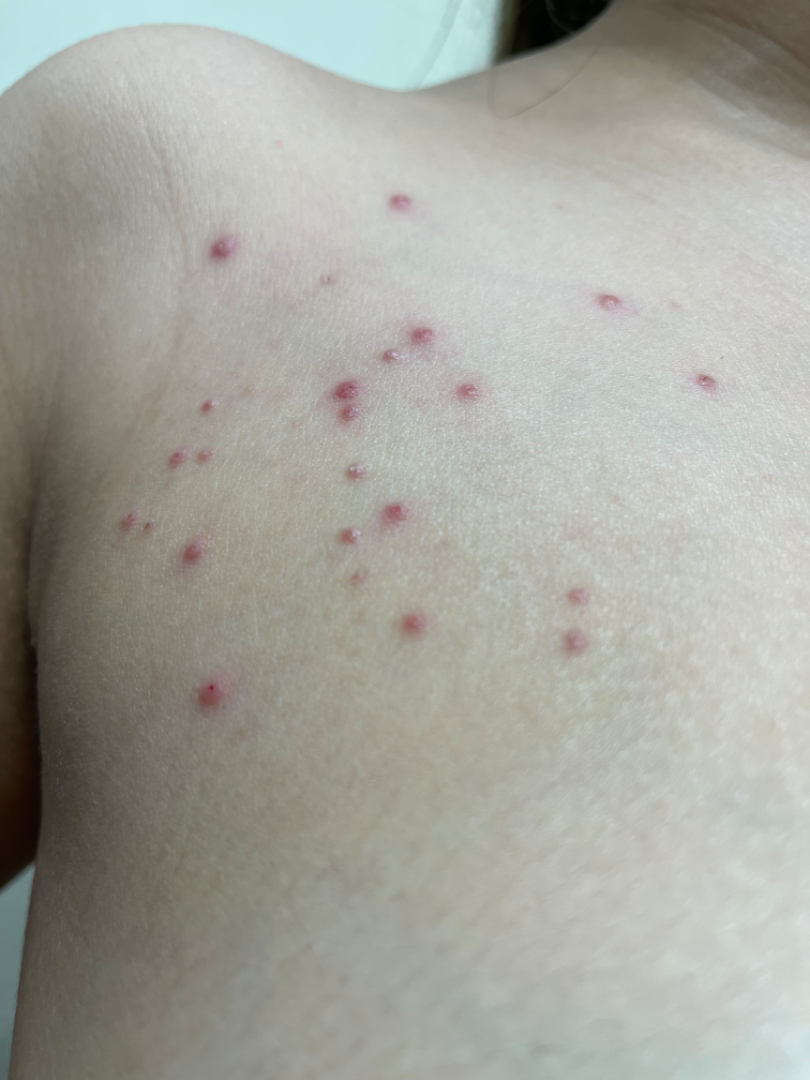On photographic review, the impression is Molluscum Contagiosum.